A close-up photograph; the affected area is the front of the torso, leg and arm: 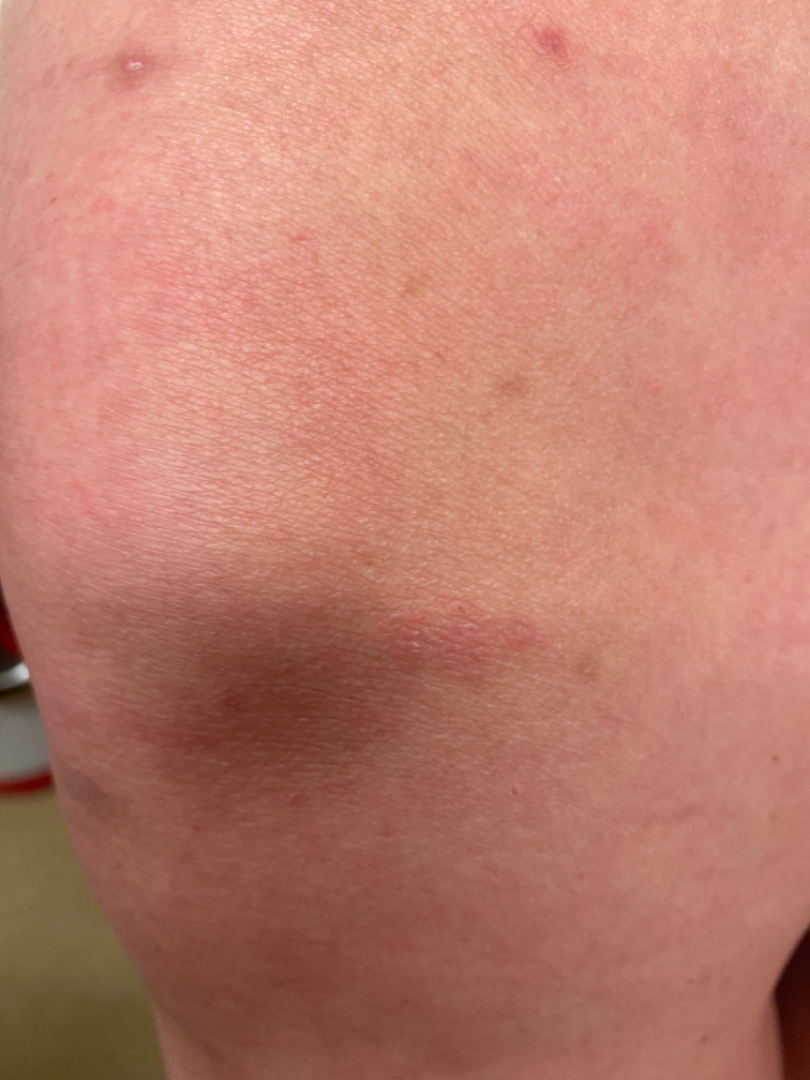Review: The reviewing dermatologist was unable to assign a differential diagnosis from the image.